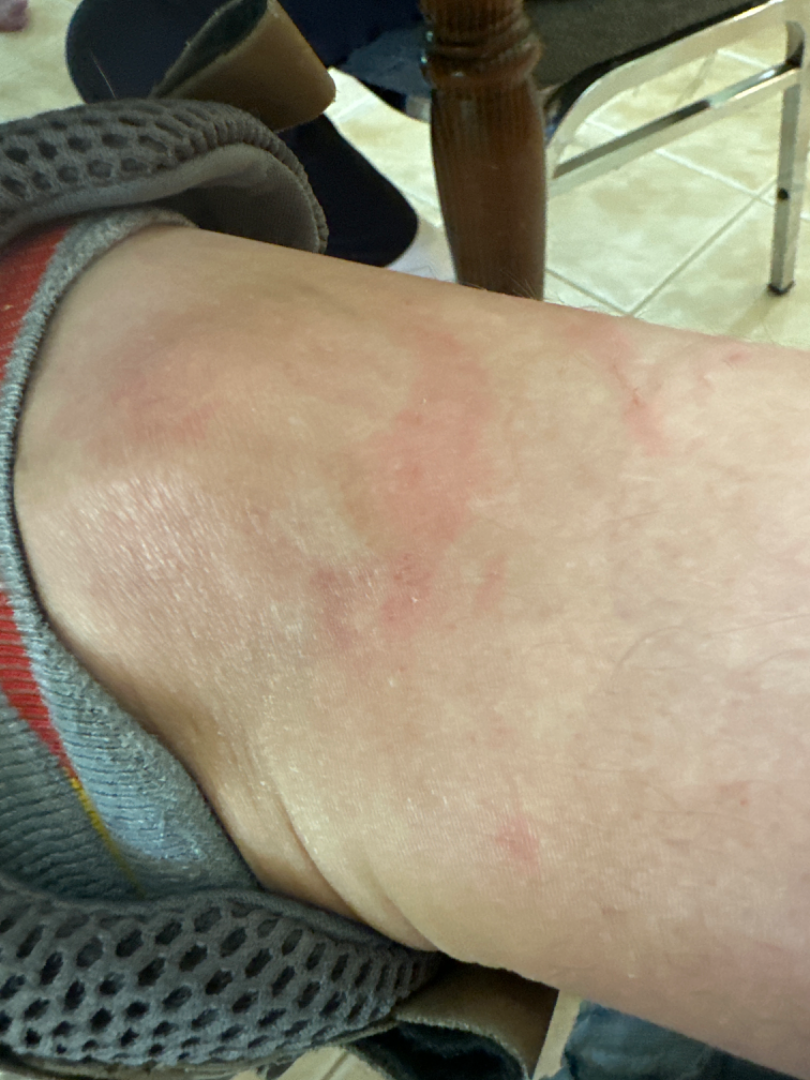Assessment: The condition could not be reliably identified from the image. Clinical context: The photograph is a close-up of the affected area.